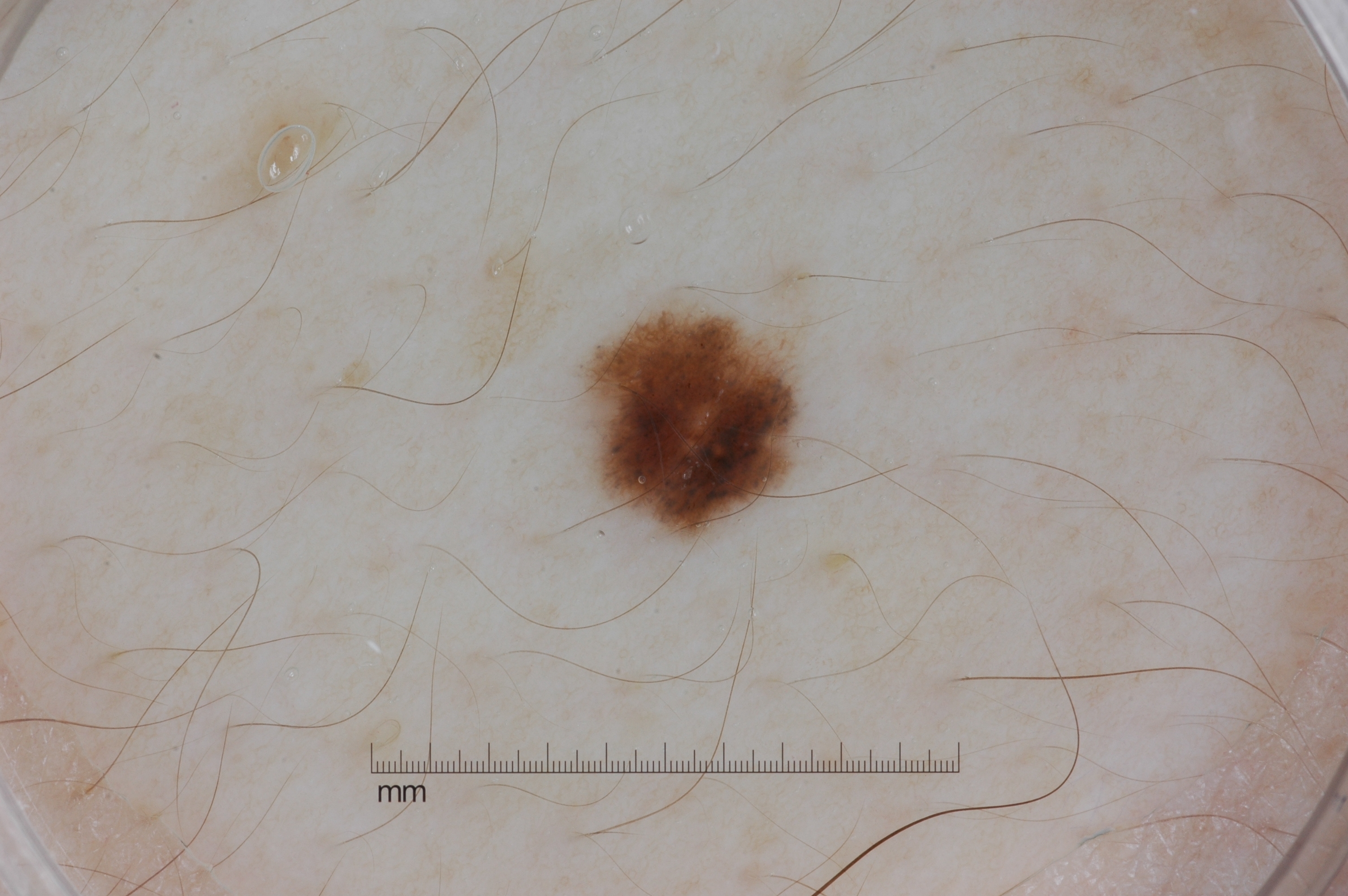This is a dermoscopic photograph of a skin lesion.
As (left, top, right, bottom), the lesion is bounded by (590, 308, 801, 532).
On dermoscopy, the lesion shows pigment network, with no streaks, milia-like cysts, or negative network.
The clinical diagnosis was a melanocytic nevus, a benign lesion.